The patient says their skin tans without first burning; collected as part of a research study, without a referral diagnosis; the patient describes having a moderate number of moles; a male patient 72 years of age: 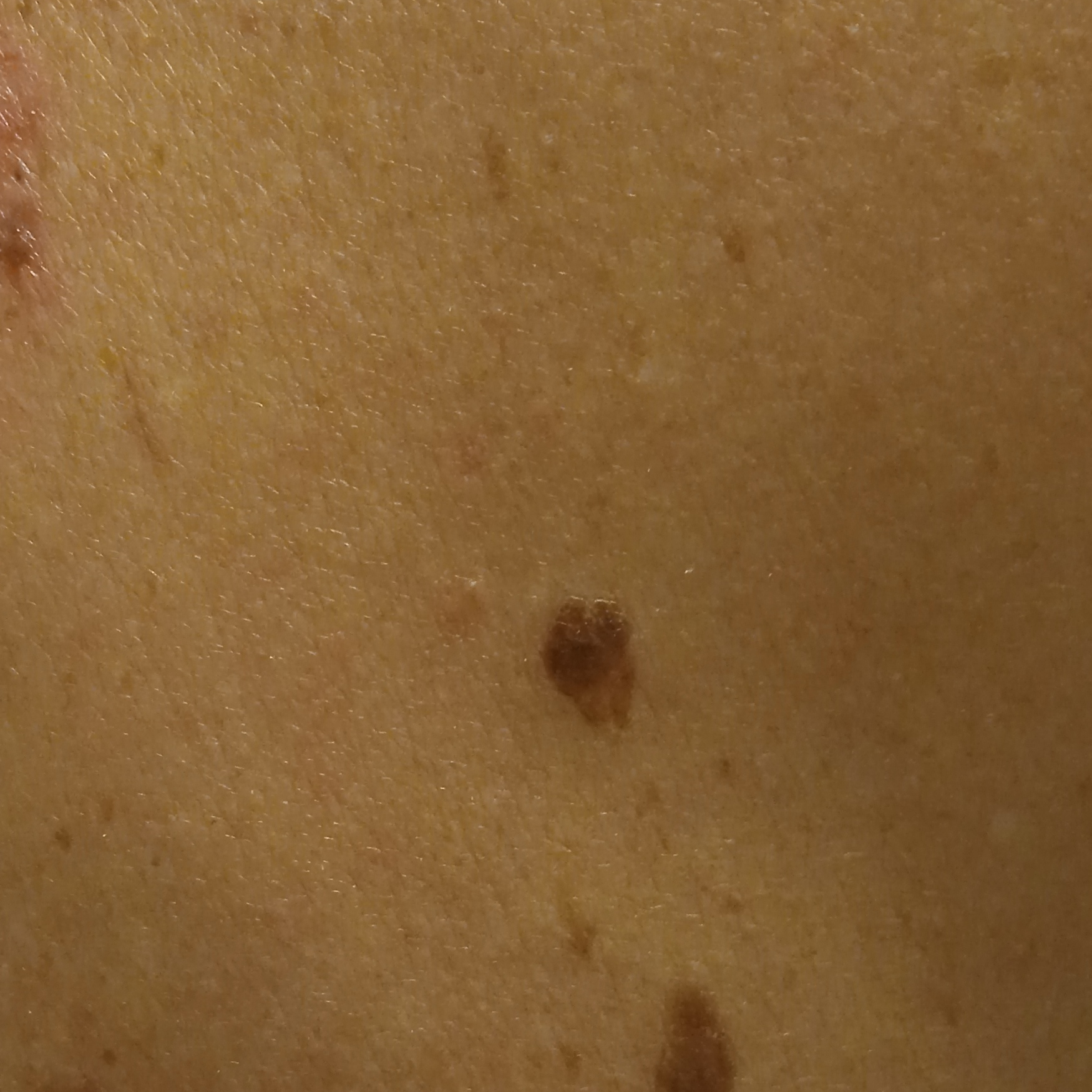Case summary: The lesion involves the back. Measuring roughly 9.6 mm. Assessment: The diagnostic impression was a seborrheic keratosis.